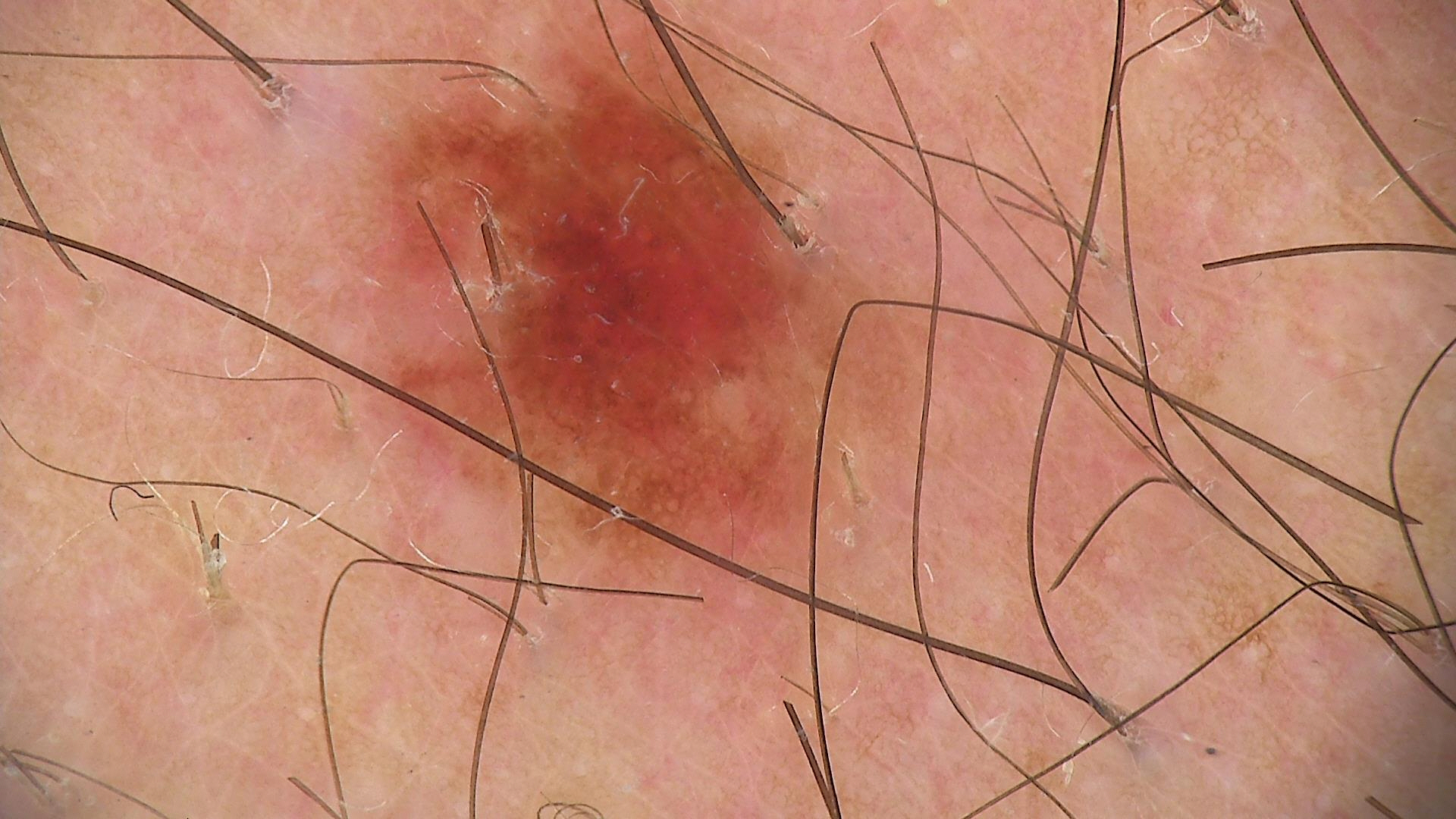  diagnosis:
    name: dysplastic junctional nevus
    code: jd
    malignancy: benign
    super_class: melanocytic
    confirmation: expert consensus